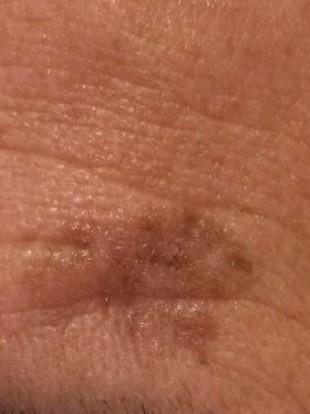pathology=Melanoma (biopsy-proven).